The lesion involves the leg; male contributor, age 18–29; the photo was captured at an angle:
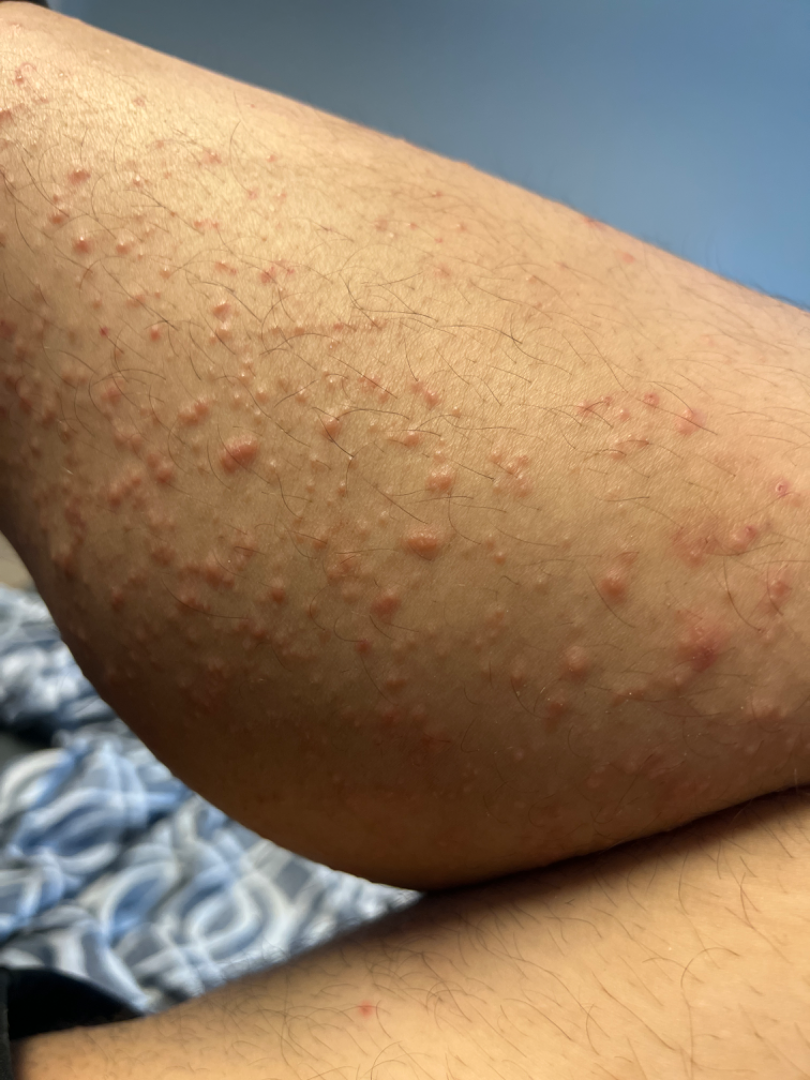On dermatologist assessment of the image, Folliculitis and Eczema were considered with similar weight.